A dermoscopy image of a single skin lesion; a female subject, in their mid- to late 40s — 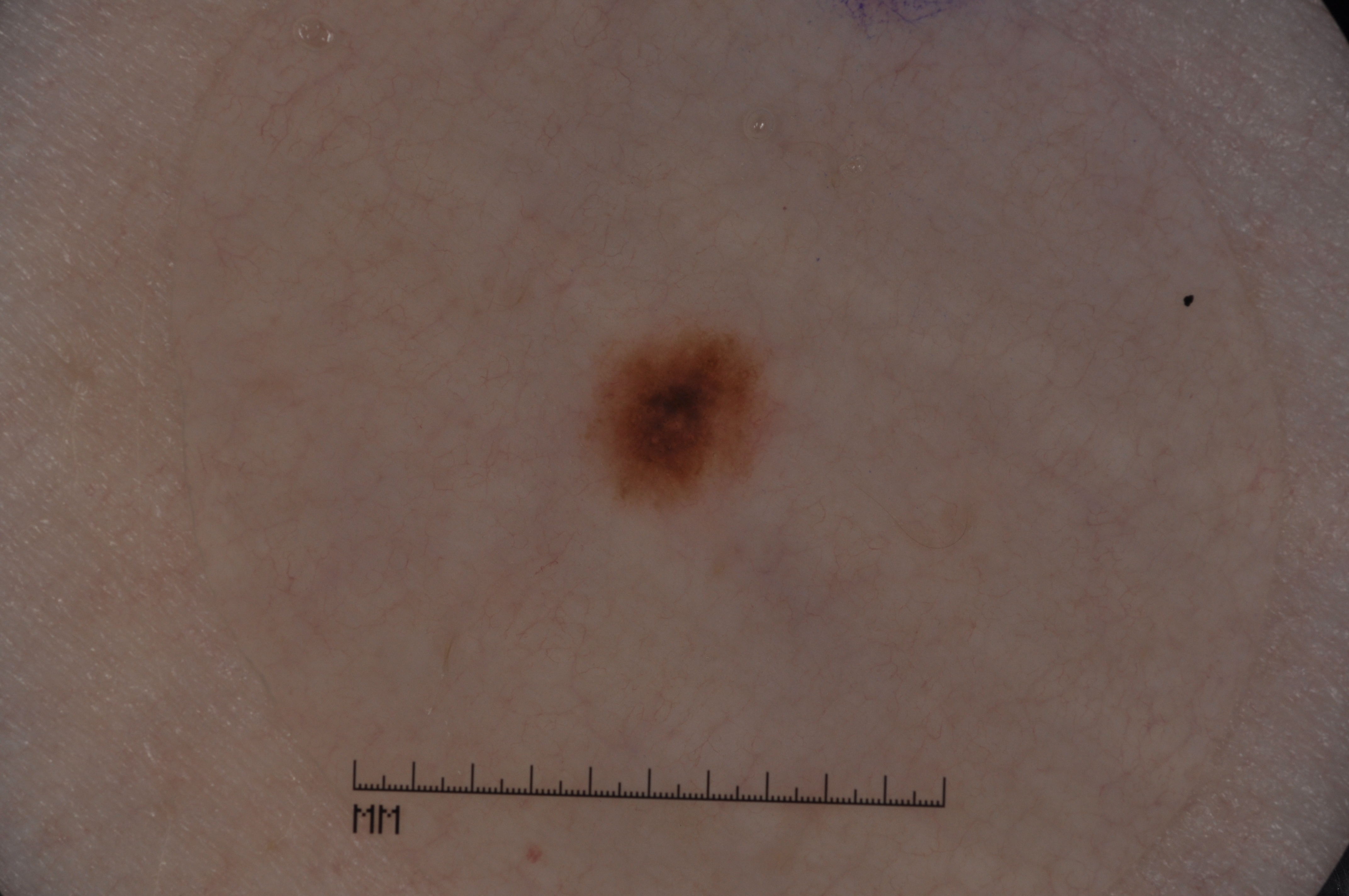dermoscopic features: pigment network; extent: small; lesion bbox: left=590, top=322, right=780, bottom=504; diagnostic label: a melanocytic nevus, a benign lesion.